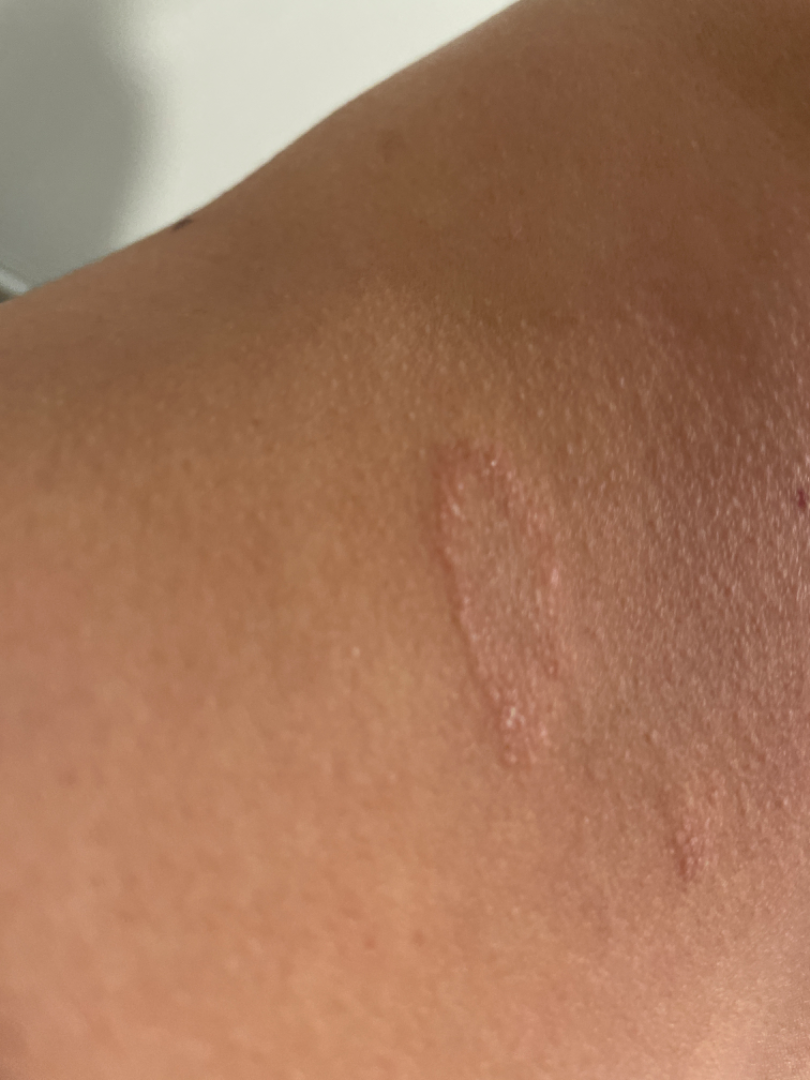Case summary:
• framing — at an angle
• diagnostic considerations — the leading impression is Pityriasis rosea; also on the differential is Tinea